The photograph is a close-up of the affected area · the contributor is a male aged 18–29 · the arm is involved.
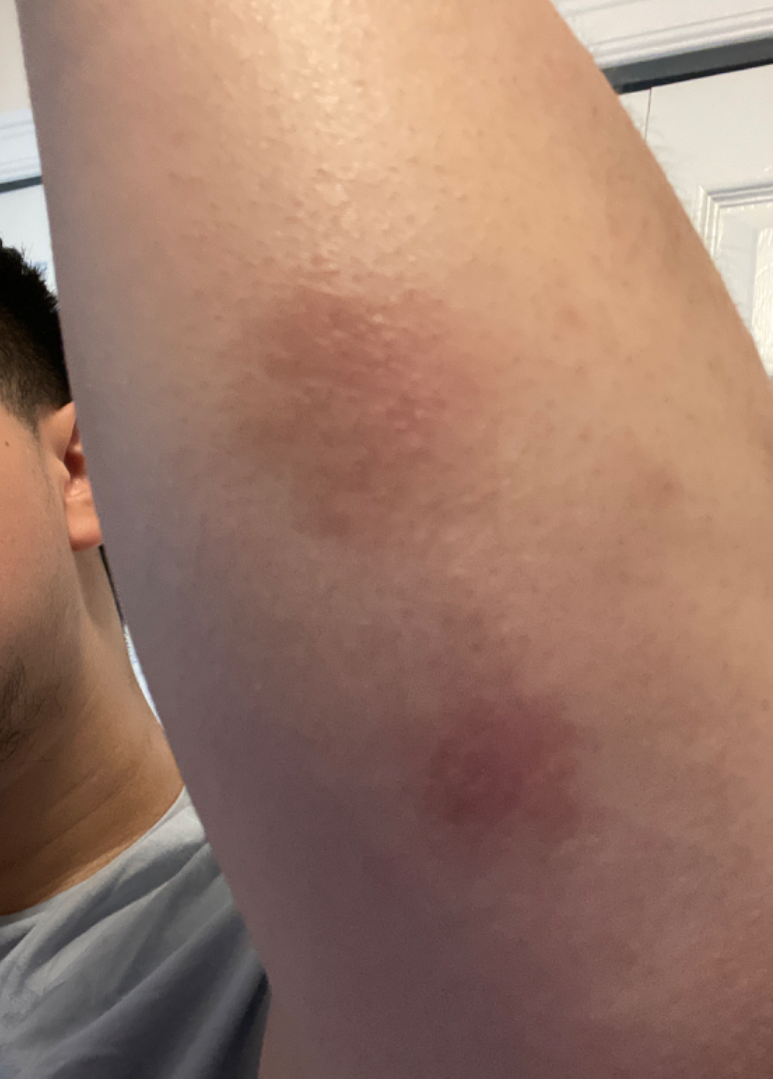| field | value |
|---|---|
| differential | the favored diagnosis is Eczema |